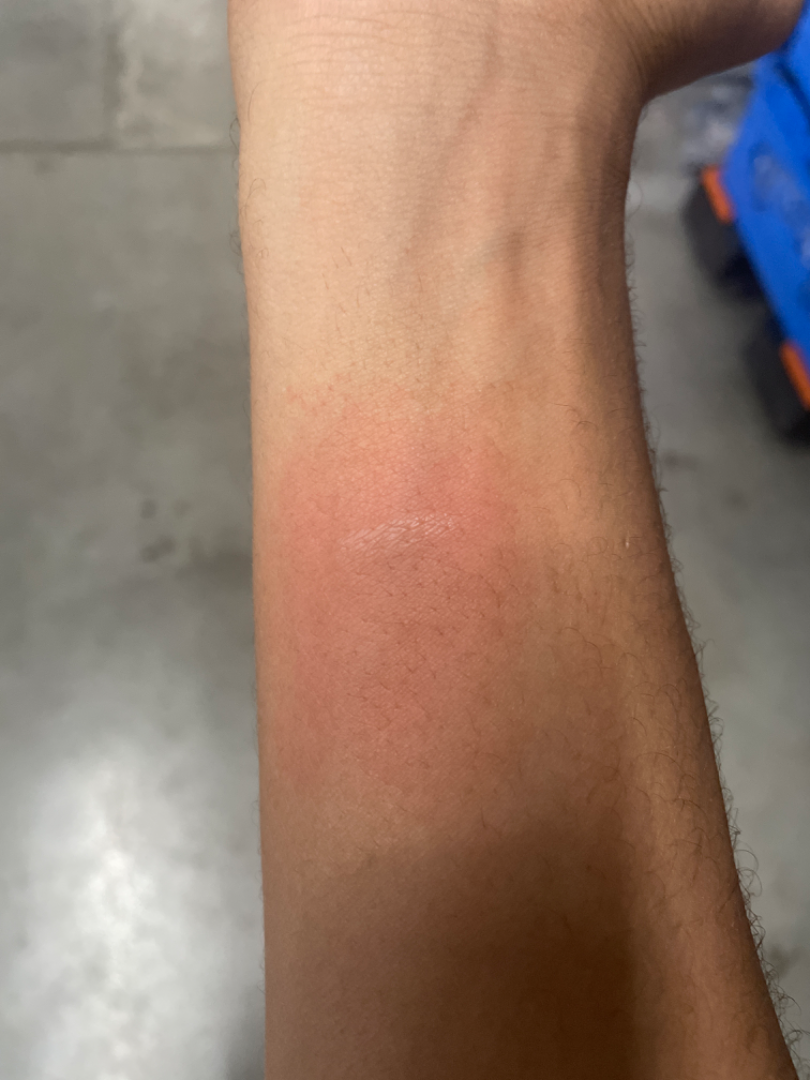assessment = indeterminate from the photograph.